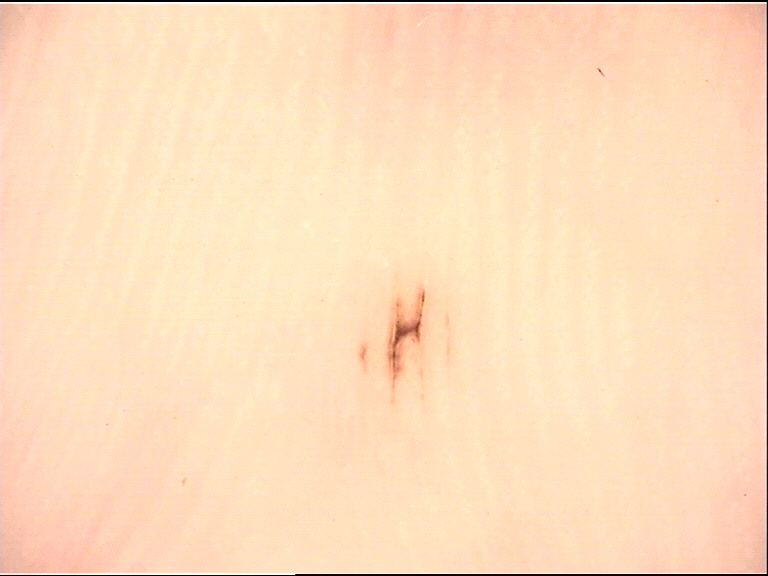category = banal, diagnosis = acral junctional nevus (expert consensus).